A clinical photo of a skin lesion taken with a smartphone · the patient was assessed as FST II.
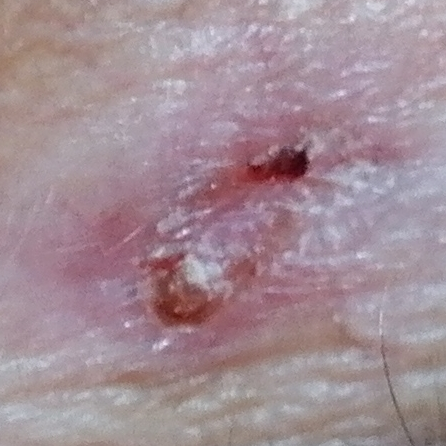diagnosis:
  name: basal cell carcinoma
  code: BCC
  malignancy: malignant
  confirmation: histopathology